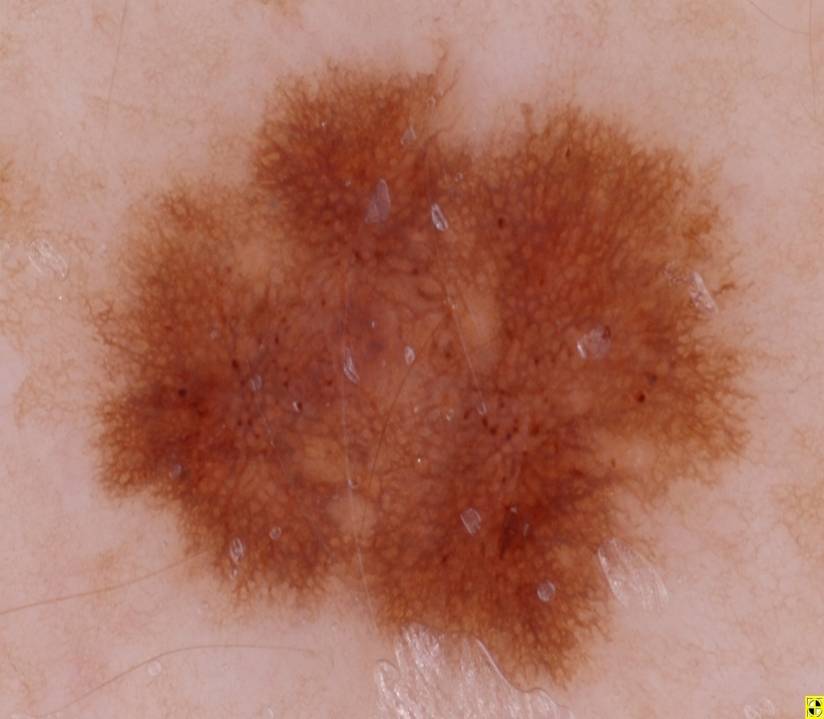{
  "image": {
    "modality": "dermoscopy"
  },
  "lesion_location": {
    "bbox_xyxy": [
      77,
      60,
      751,
      688
    ]
  },
  "dermoscopic_features": {
    "present": [
      "pigment network",
      "globules"
    ],
    "absent": [
      "negative network",
      "milia-like cysts",
      "streaks"
    ]
  },
  "lesion_extent": {
    "approx_field_fraction_pct": 51
  },
  "diagnosis": {
    "name": "melanocytic nevus",
    "malignancy": "benign",
    "lineage": "melanocytic",
    "provenance": "clinical"
  }
}